The subject is a female aged 43-47, a dermoscopic close-up of a skin lesion — 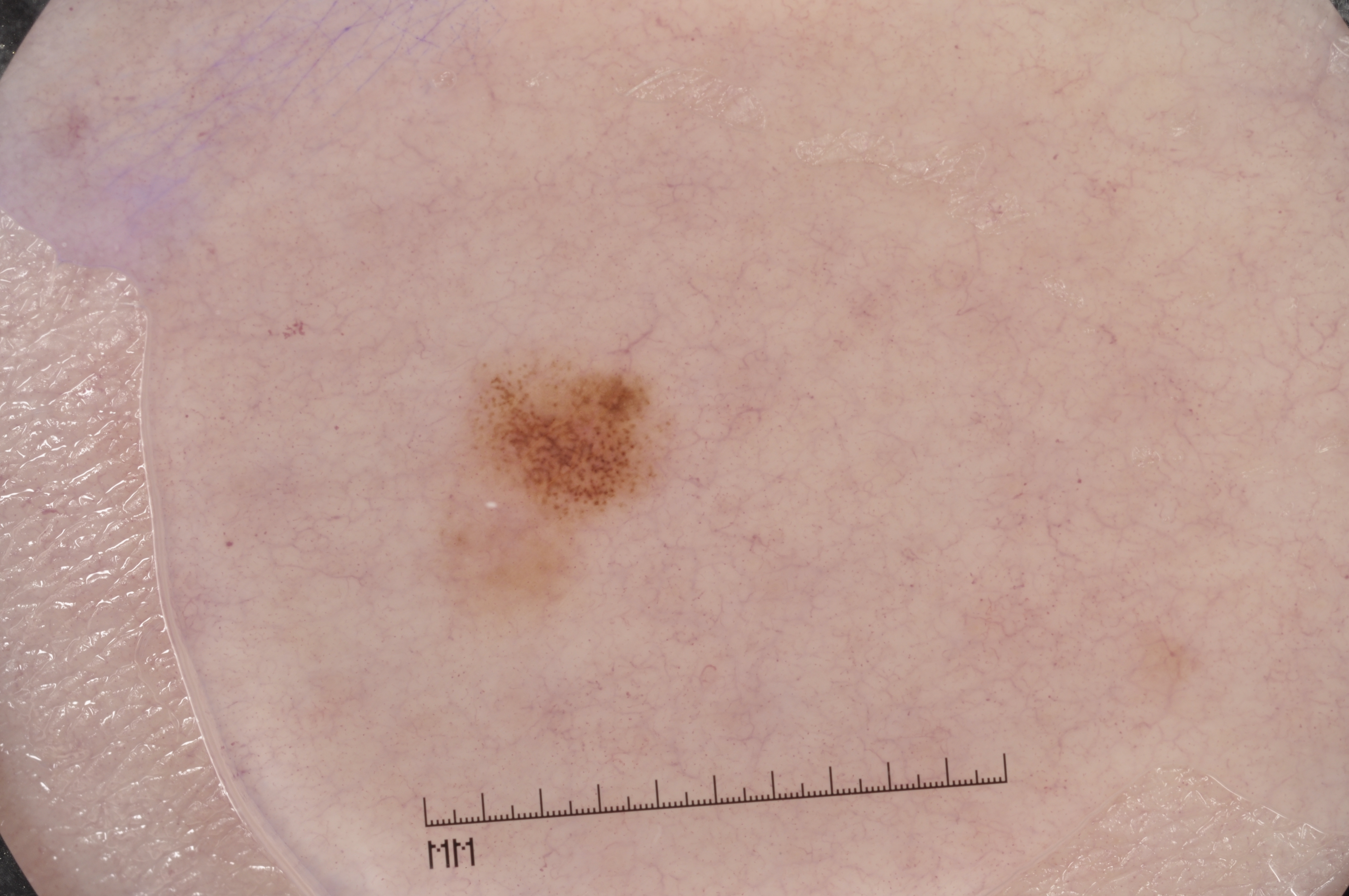Findings: The dermoscopic pattern shows milia-like cysts and pigment network, with no streaks or negative network. With coordinates (x1, y1, x2, y2), the lesion is bounded by bbox(453, 357, 664, 595). Assessment: Diagnosed as a melanocytic nevus.